Fitzpatrick II; lay graders estimated Monk skin tone scale 2 or 3 (two reviewer pools), the photograph is a close-up of the affected area — 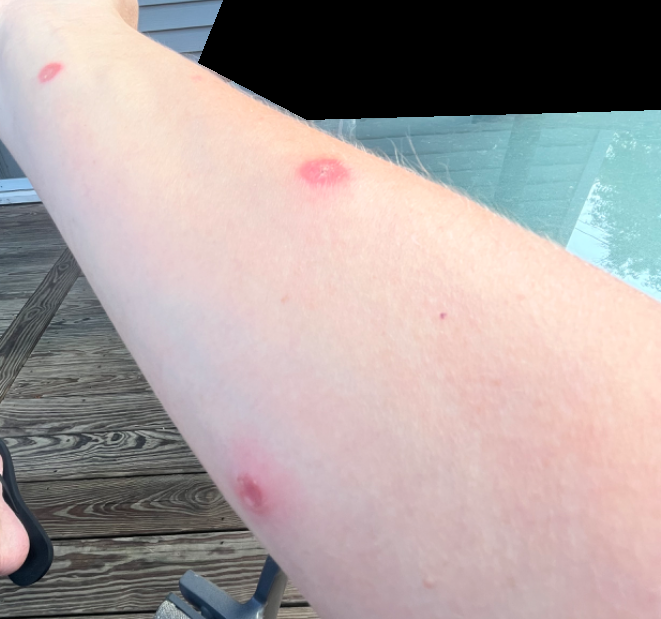  differential:
    leading:
      - Impetigo
    considered:
      - Insect Bite
    unlikely:
      - Eczema